The photograph is a close-up of the affected area. The head or neck is involved — 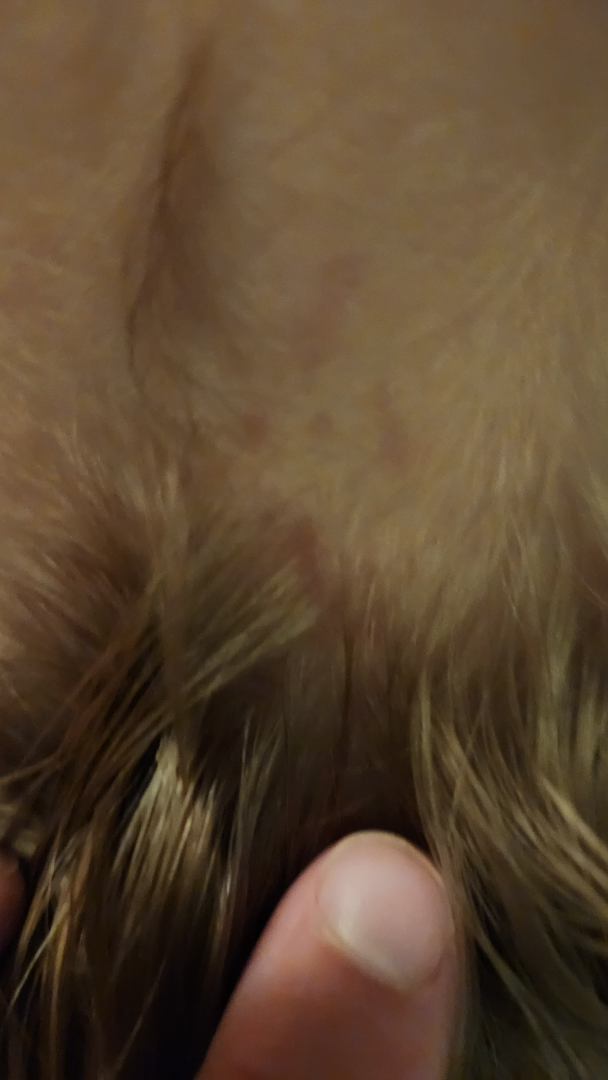Findings: No differential diagnosis could be assigned on photographic review.